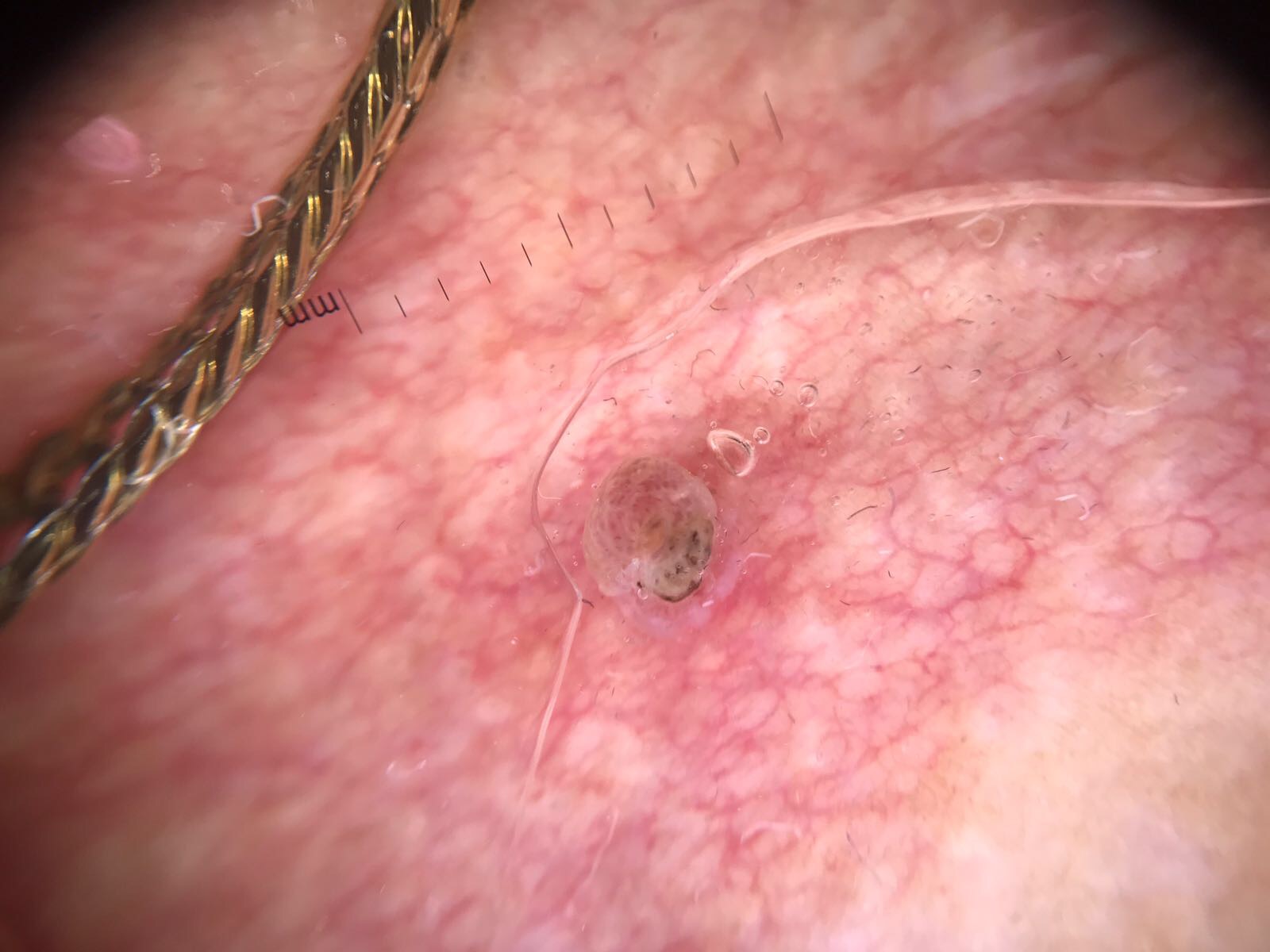| key | value |
|---|---|
| image | dermoscopy |
| category | keratinocytic |
| label | squamous cell carcinoma (biopsy-proven) |